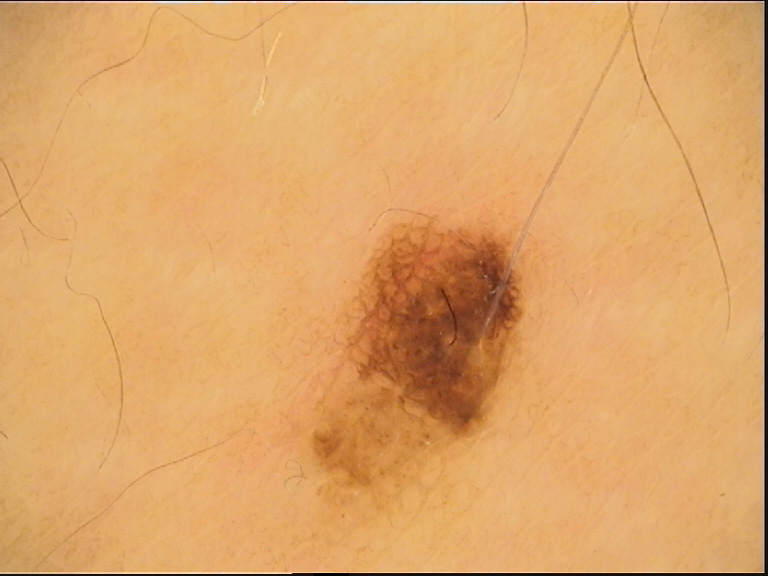A dermoscopic photograph of a skin lesion.
The diagnosis was a dysplastic junctional nevus.